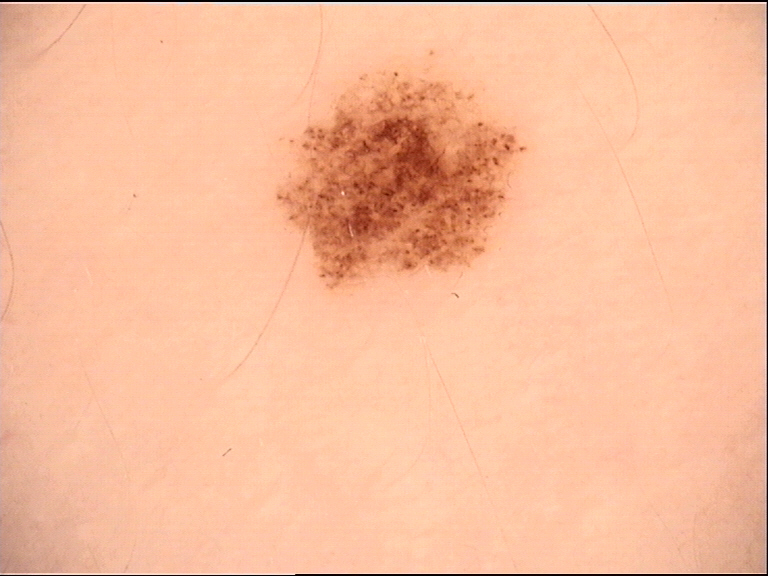Case:
A skin lesion imaged with a dermatoscope.
Impression:
Consistent with a dysplastic junctional nevus.